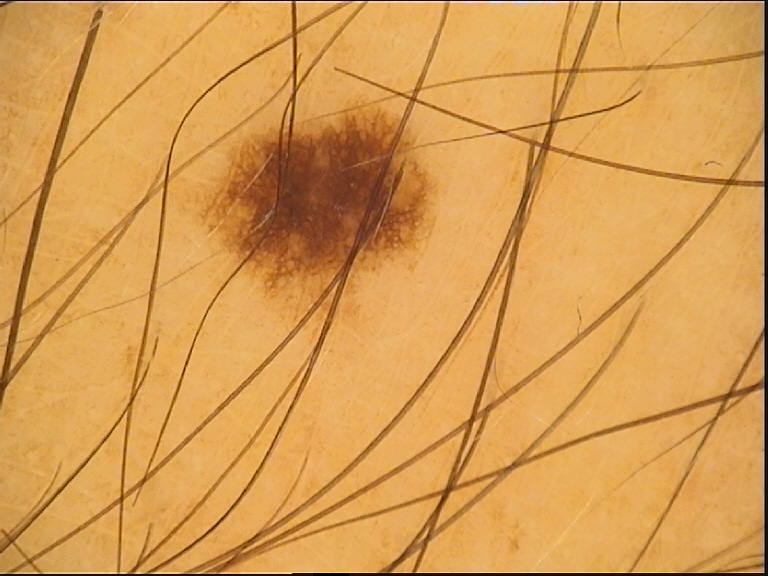A dermoscopy image of a single skin lesion. Classified as a junctional nevus.